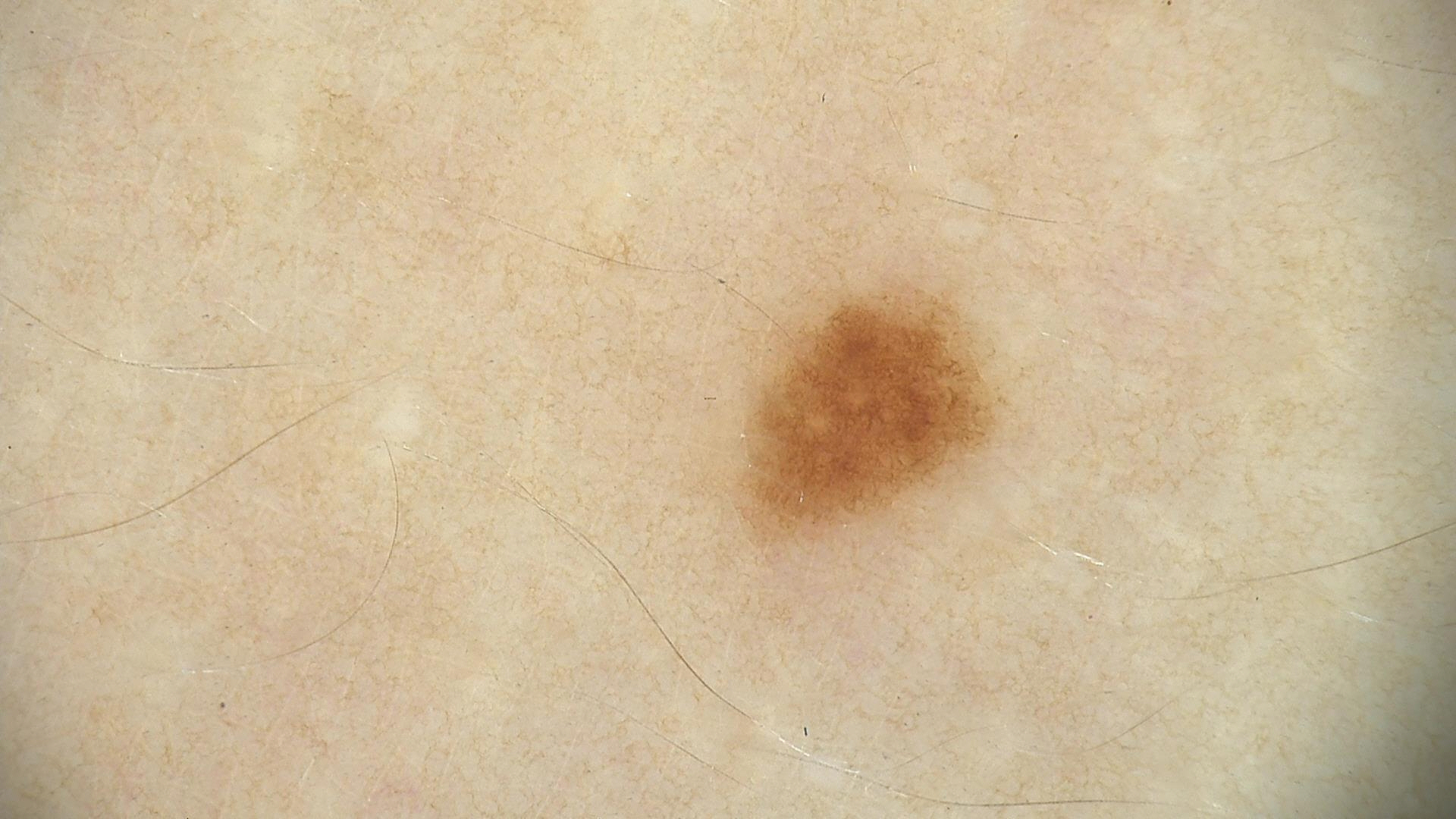* label: dysplastic junctional nevus (expert consensus)